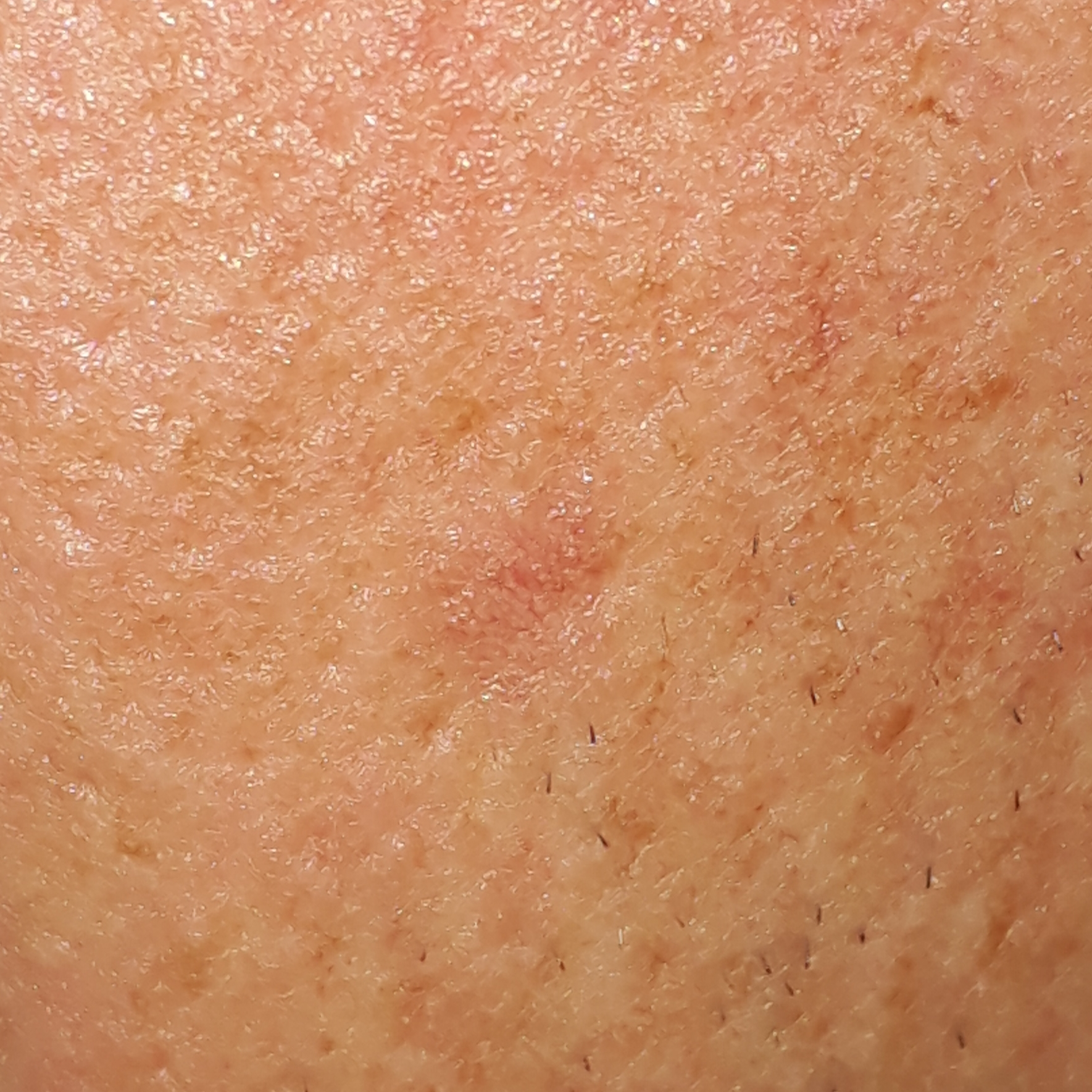A clinical photograph showing a skin lesion. The lesion was found on the face. Per patient report, the lesion itches and has grown. The diagnostic impression was an actinic keratosis.